This is a close-up image; the lesion involves the head or neck:
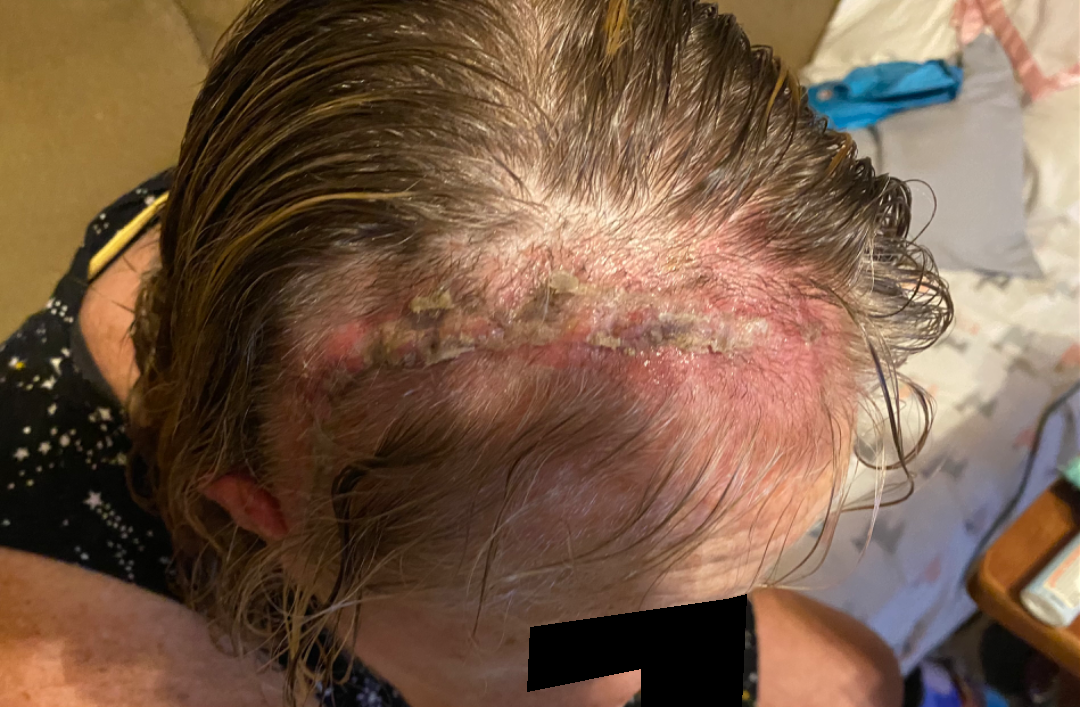<summary>
<assessment>indeterminate</assessment>
</summary>